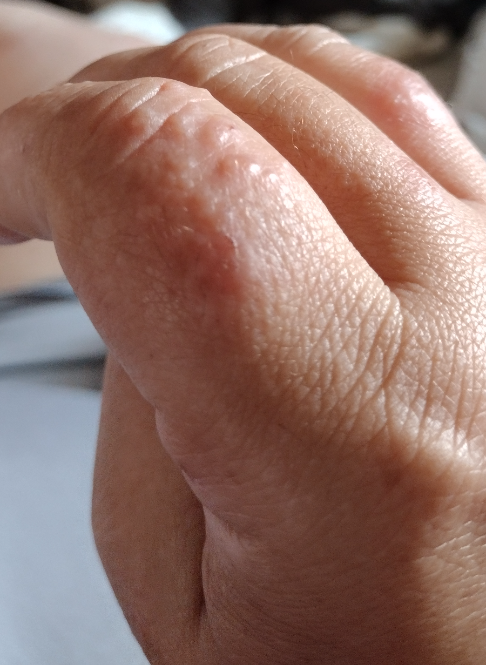assessment = indeterminate from the photograph | view = at an angle | patient = female, age 30–39 | body site = arm, back of the hand and leg.